The affected area is the back of the hand, leg and arm; a close-up photograph: 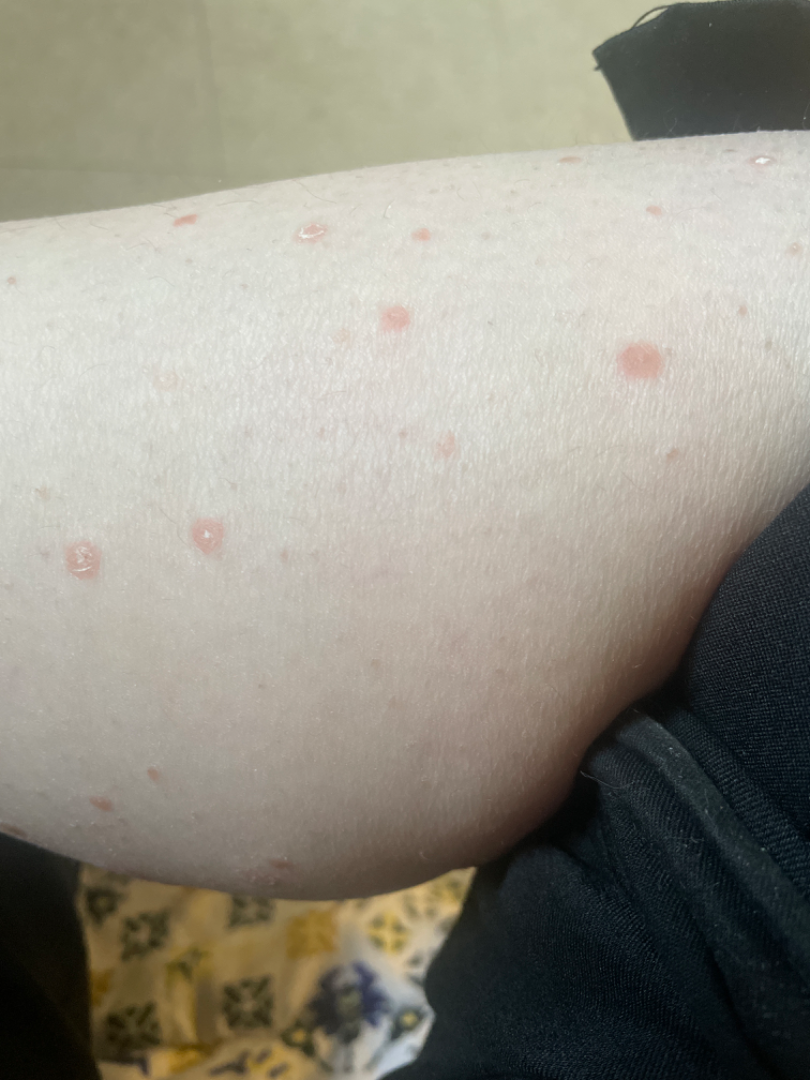systemic_symptoms: none reported
symptoms: itching
texture: rough or flaky
skin_tone:
  fitzpatrick: II
duration: one to four weeks
differential:
  leading:
    - Psoriasis